Dermoscopy of a skin lesion.
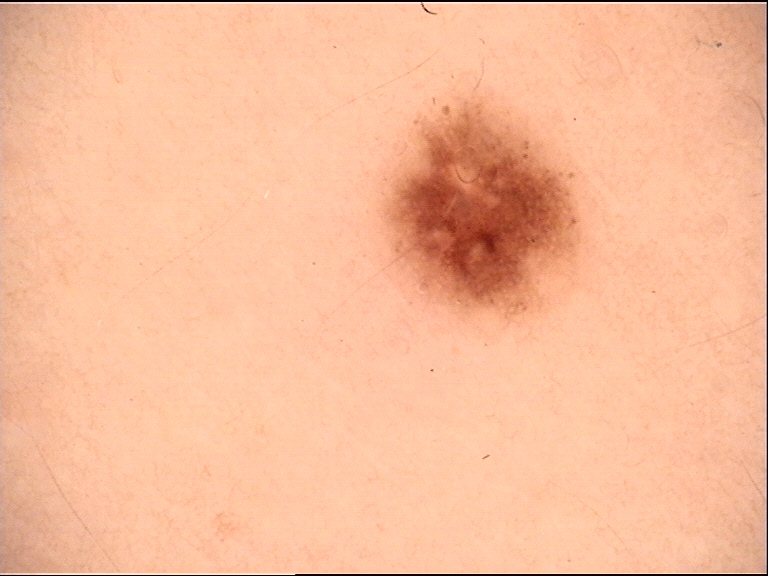Labeled as a benign lesion — a dysplastic junctional nevus.